Located on the head or neck; the photograph was taken at an angle:
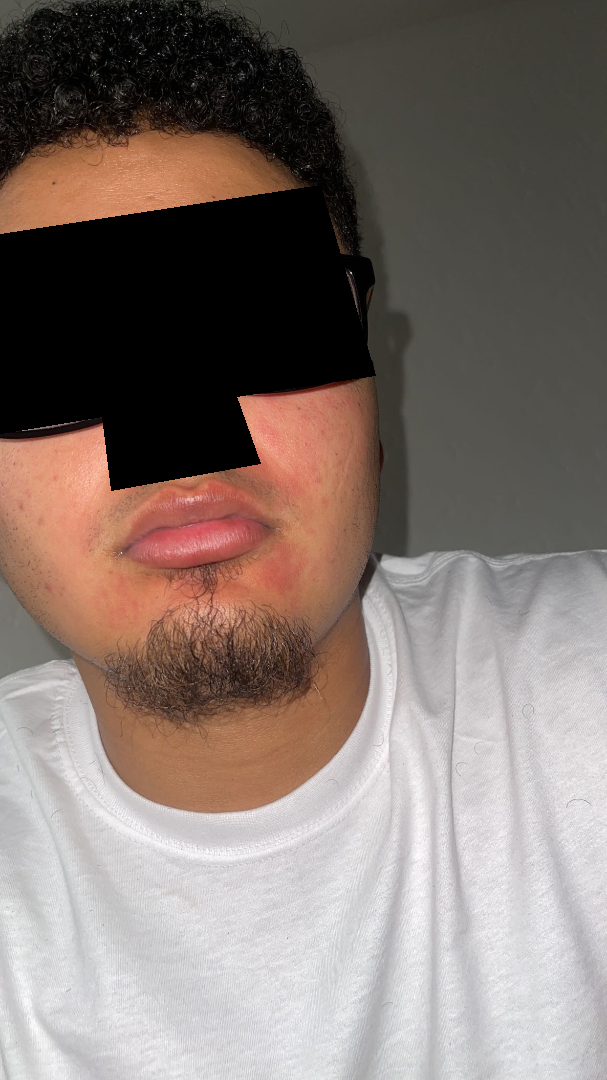| feature | finding |
|---|---|
| symptoms | bothersome appearance |
| patient describes the issue as | a rash |
| associated systemic symptoms | none reported |
| present for | three to twelve months |
| lesion texture | flat |
| diagnostic considerations | one reviewing dermatologist: the differential, in no particular order, includes Acne, Rosacea and Perioral Dermatitis |